This is a close-up image; the lesion is described as raised or bumpy; located on the head or neck — 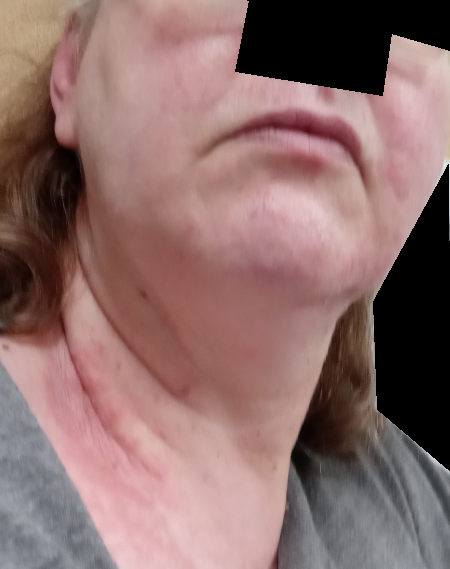Assessment: Diagnostic features were not clearly distinguishable in this photograph.